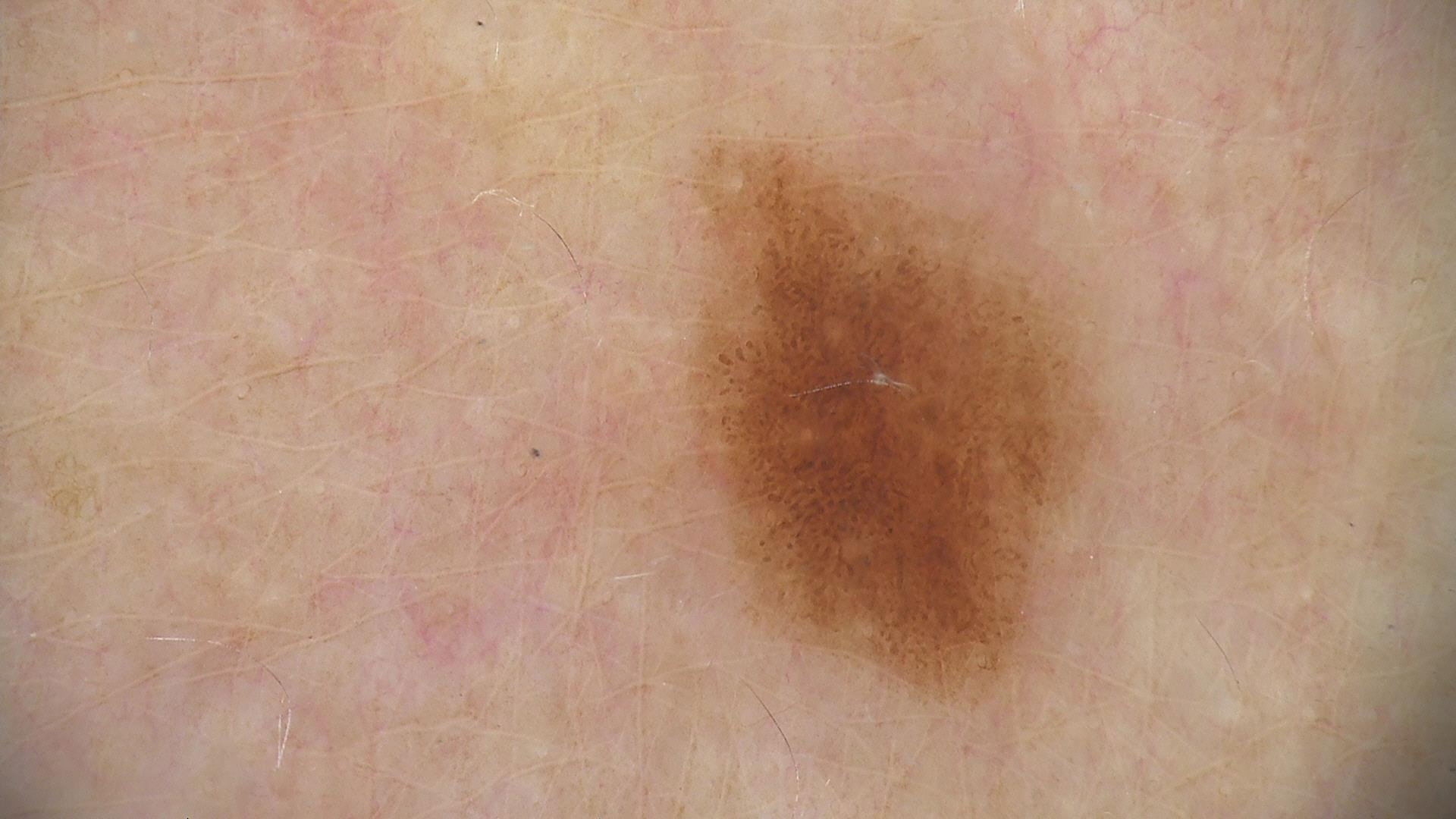label = dysplastic junctional nevus (expert consensus).